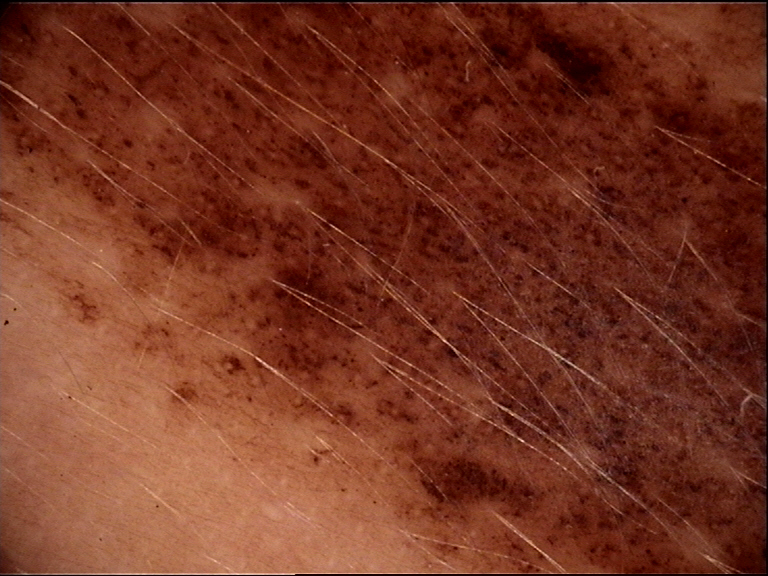Q: What is the imaging modality?
A: dermoscopy
Q: What is the diagnosis?
A: congenital compound nevus (expert consensus)